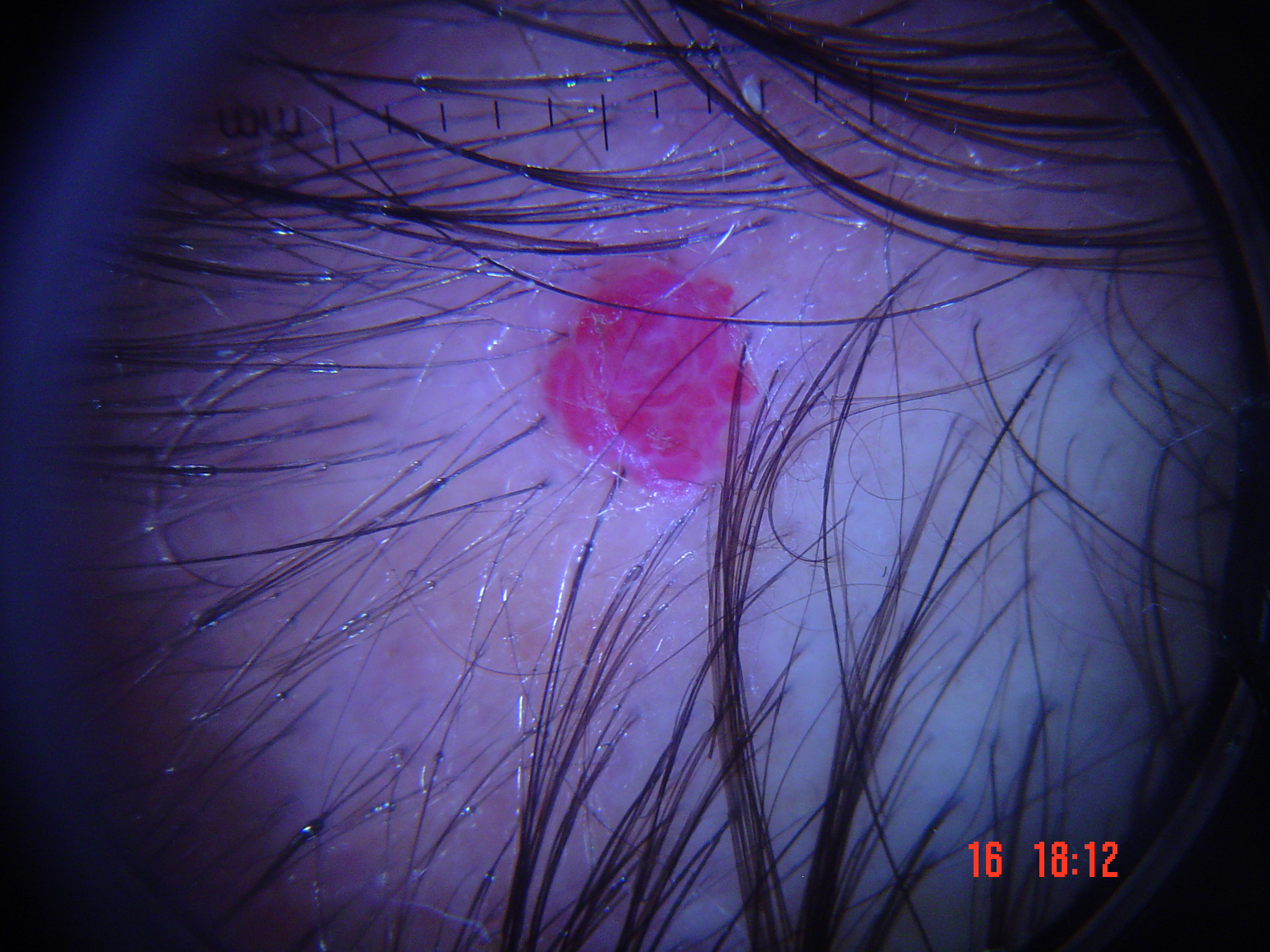The morphology is that of a vascular lesion.
Classified as a hemangioma.